Imaged for a research study, with no referral diagnosis recorded · a female patient aged 26 · a dermoscopy image of a skin lesion:
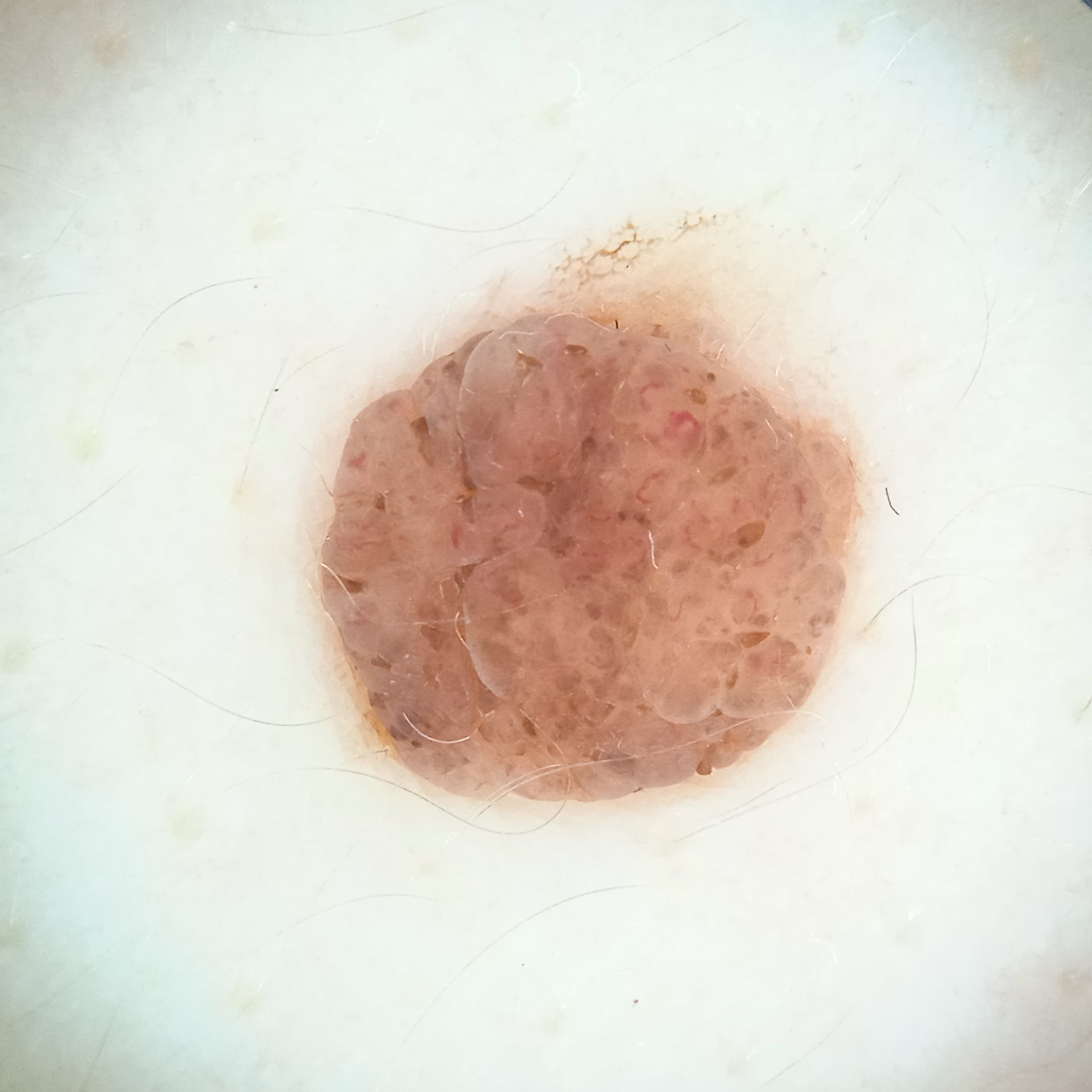- location: the back
- diameter: 5.6 mm
- diagnosis: melanocytic nevus (dermatologist consensus)